Reported duration is three to twelve months · the lesion is described as rough or flaky · the lesion is associated with bothersome appearance · the patient considered this skin that appeared healthy to them · close-up view · the lesion involves the head or neck and back of the torso:
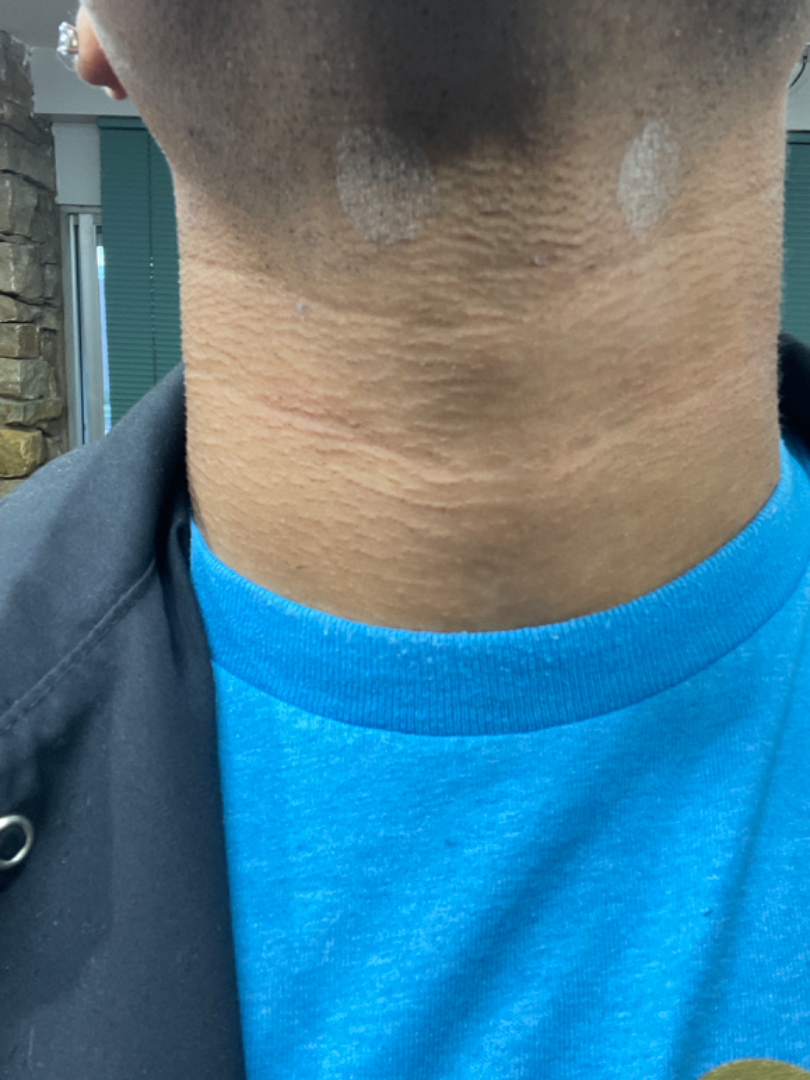The case was difficult to assess from the available photograph.